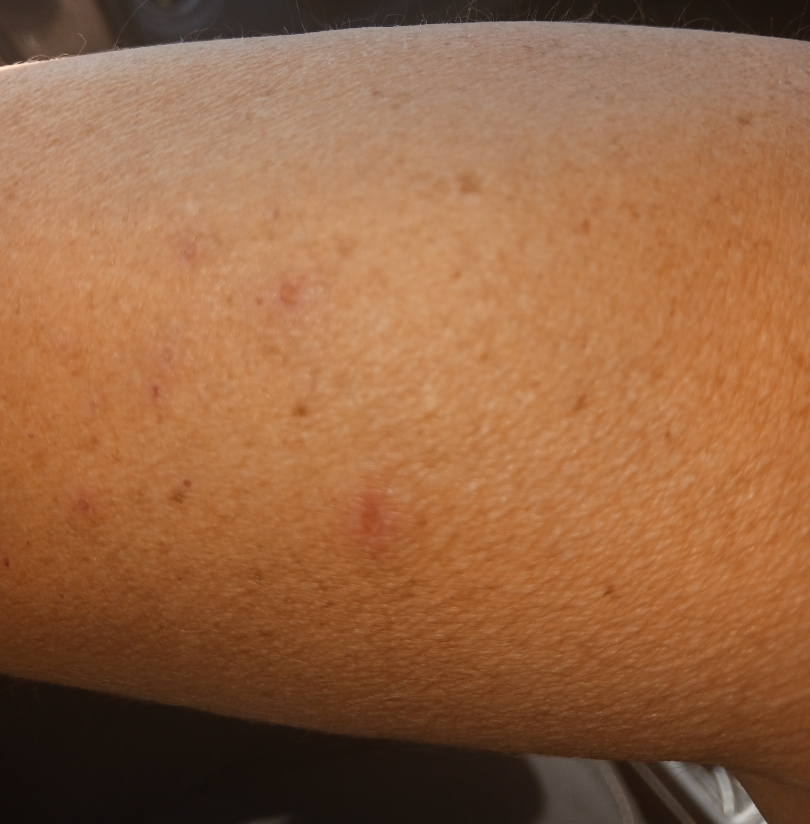{"assessment": "indeterminate", "body_site": ["arm", "back of the torso", "back of the hand", "front of the torso"], "shot_type": "close-up"}